Dermoscopy of a skin lesion · a female subject, aged 38 to 42.
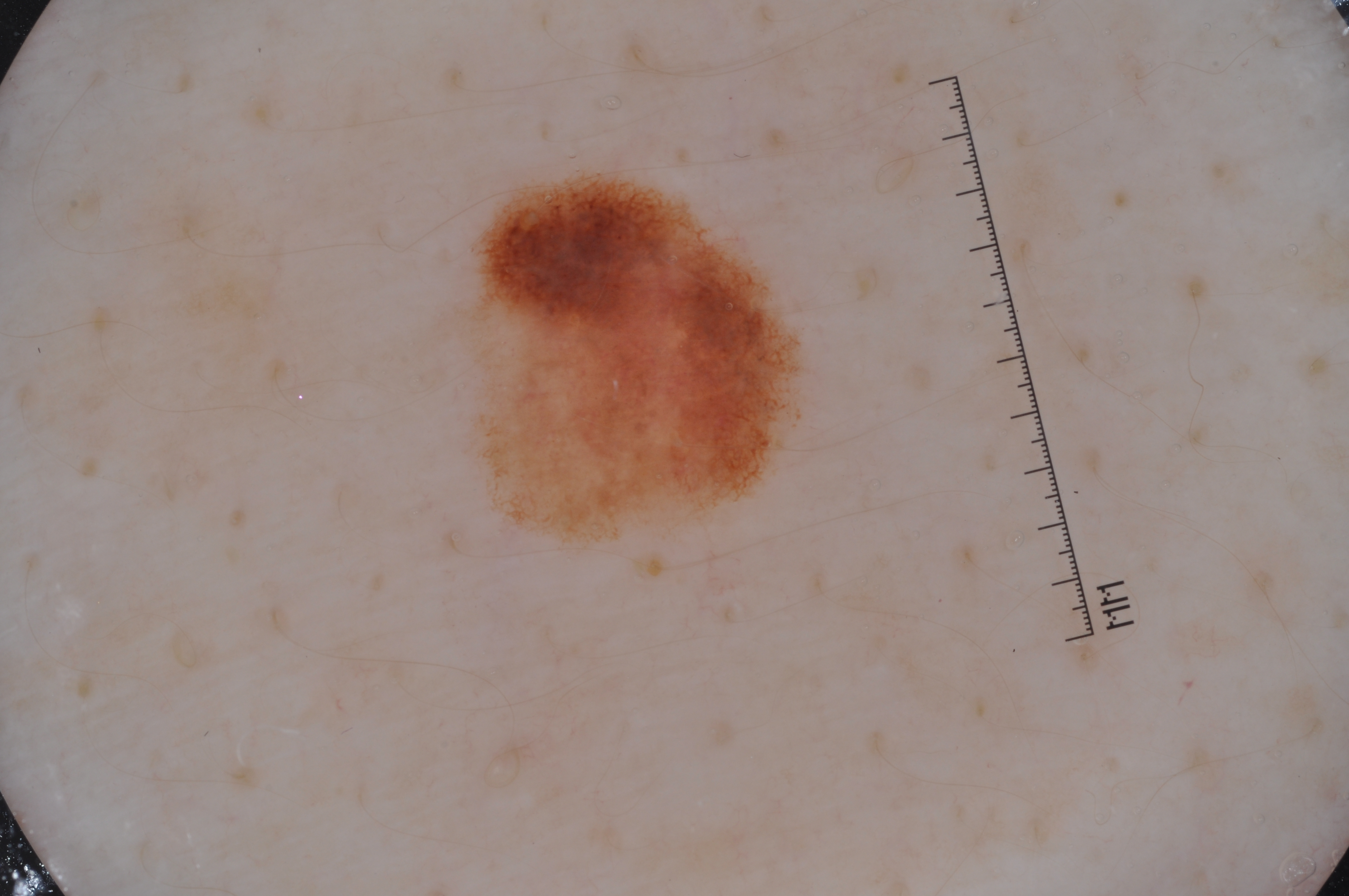Dermoscopic review identifies pigment network.
The lesion occupies the region 467/170/810/543.
The lesion occupies roughly 8% of the field.
The clinical diagnosis was a melanocytic nevus.